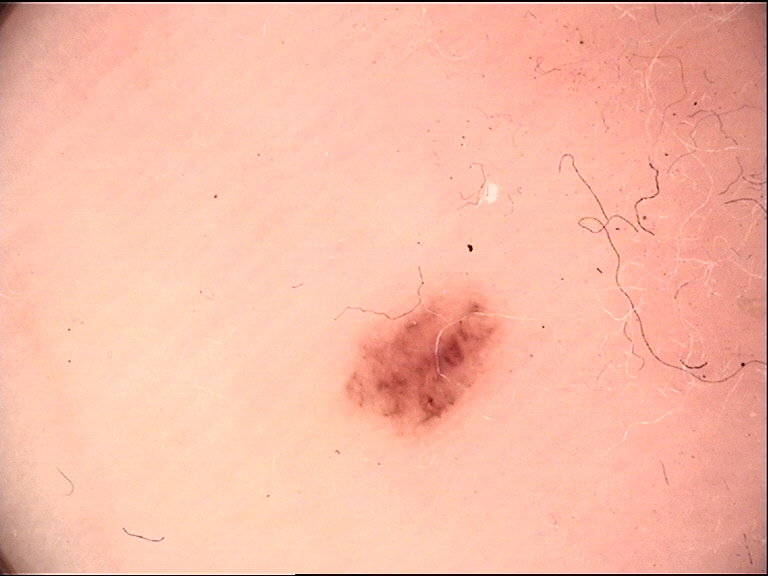imaging: dermatoscopy | class: acral junctional nevus (expert consensus).